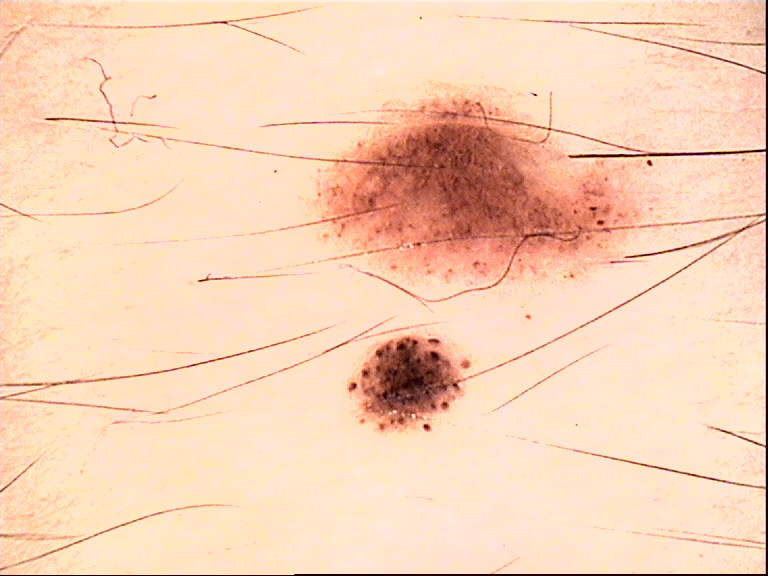Impression:
The diagnostic label was a dysplastic junctional nevus.